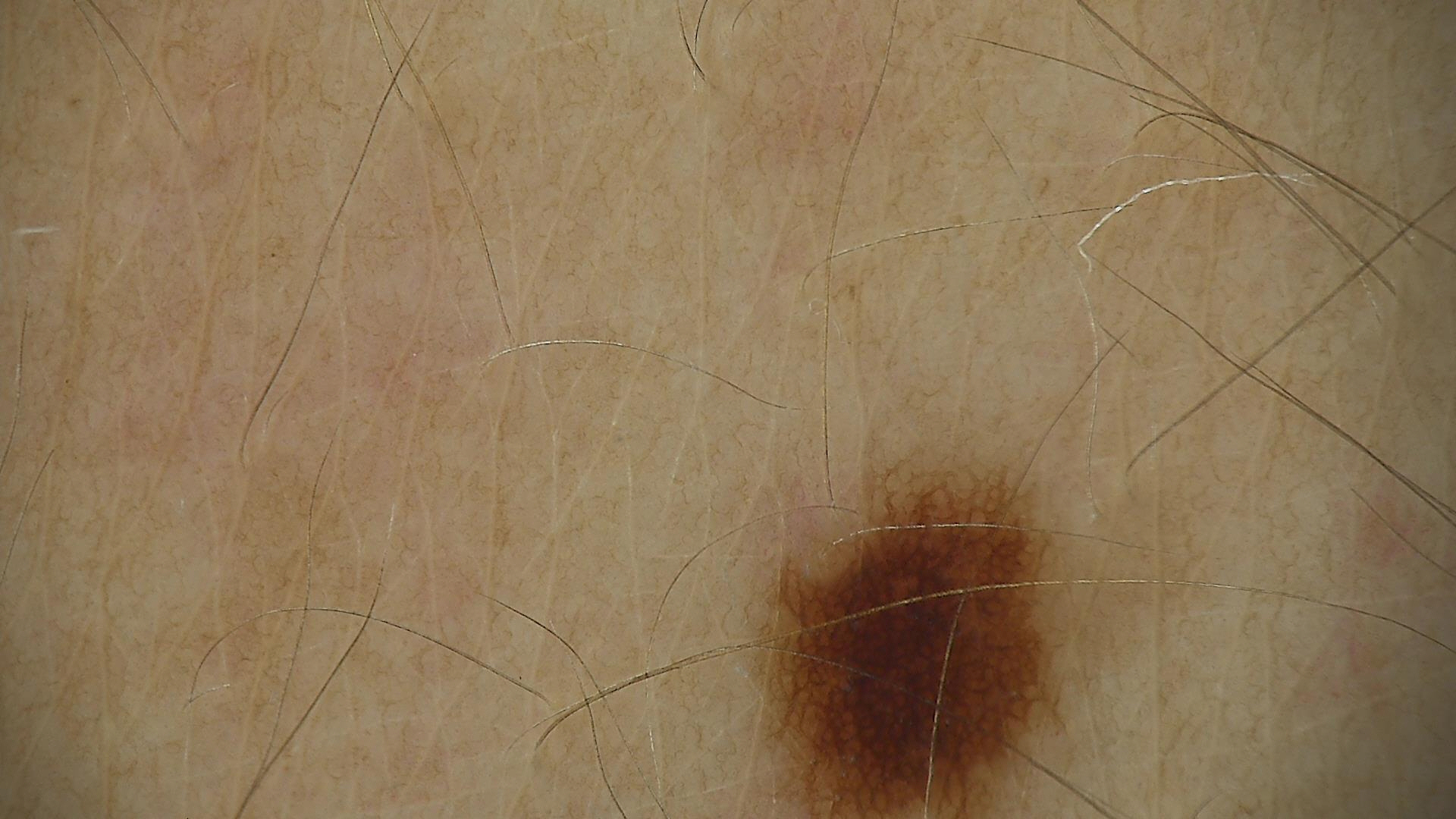Findings:
– image type: dermoscopy
– class: dysplastic junctional nevus (expert consensus)